A dermoscopy image of a single skin lesion:
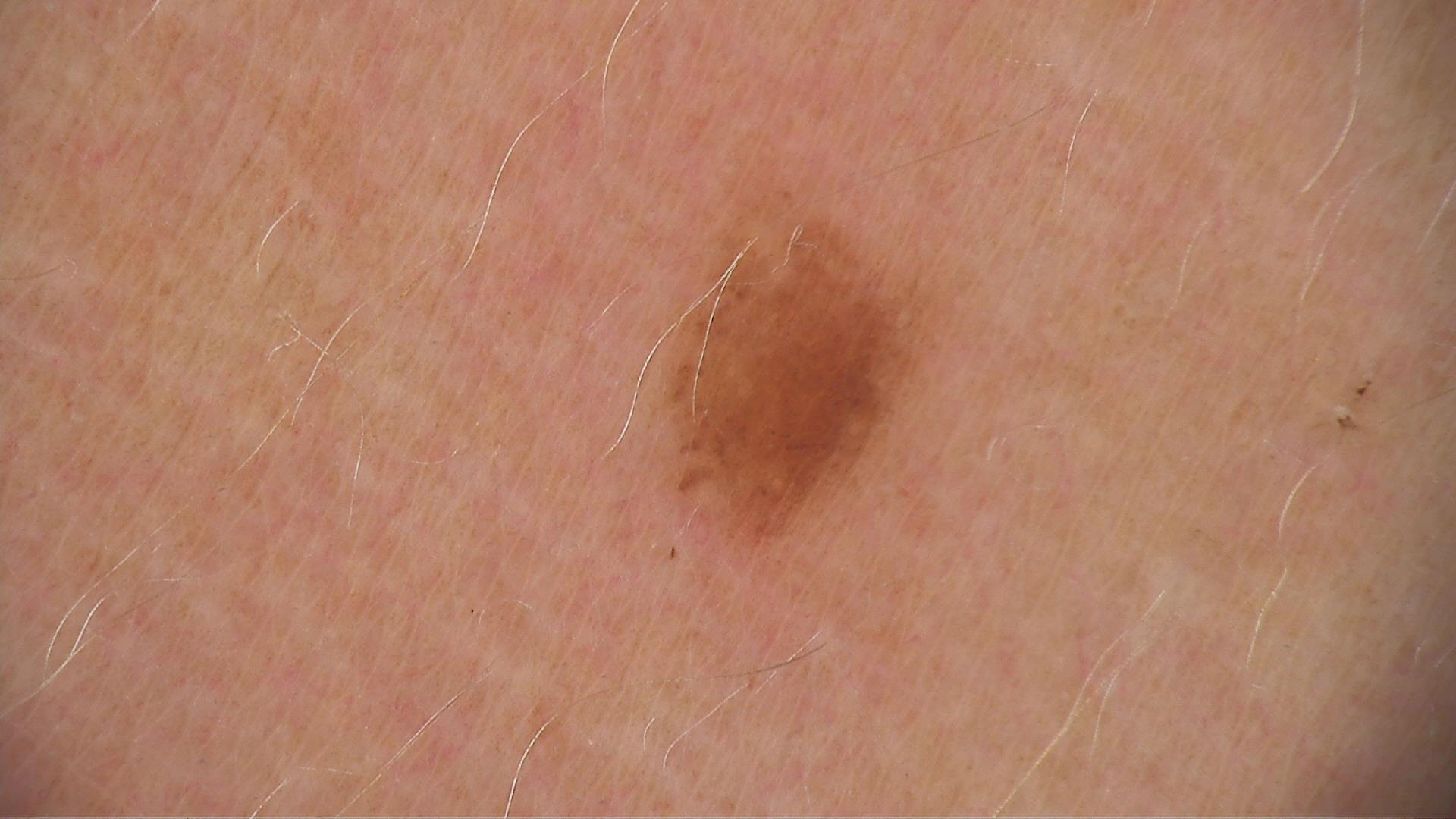{
  "diagnosis": {
    "name": "dysplastic junctional nevus",
    "code": "jd",
    "malignancy": "benign",
    "super_class": "melanocytic",
    "confirmation": "expert consensus"
  }
}